An image taken at a distance. The affected area is the leg. Male contributor, age 30–39:
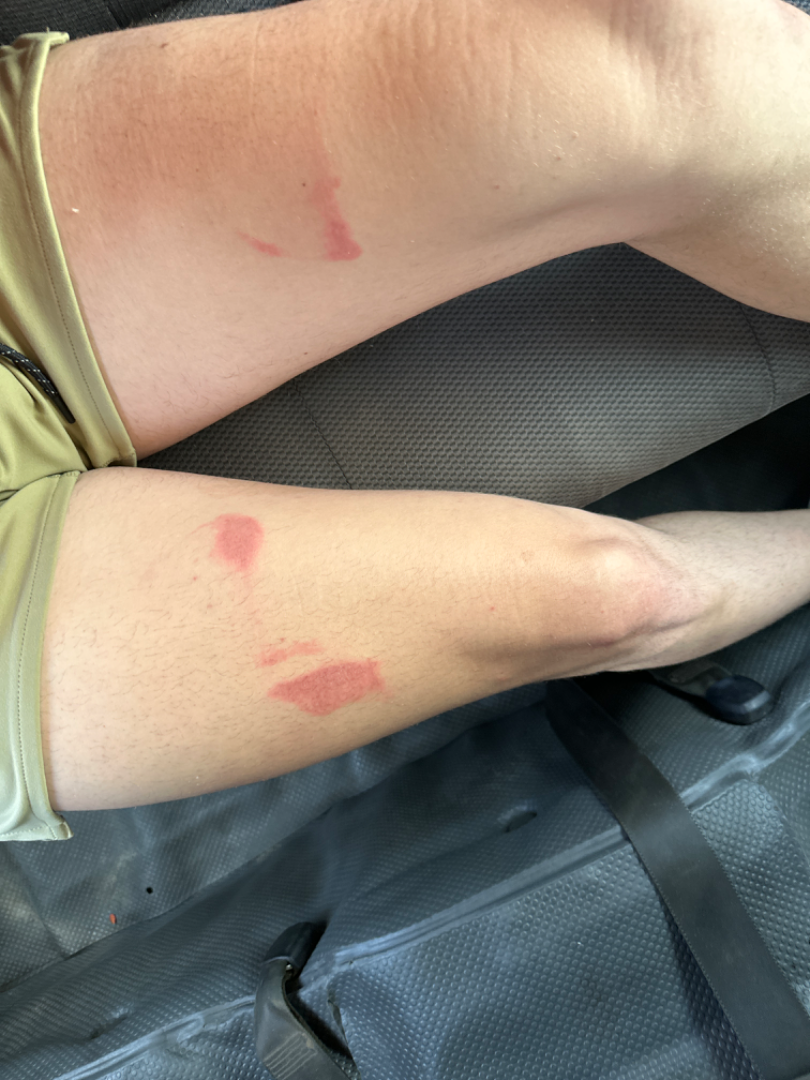- impression · the differential includes Abrasion and/or friction burn of thigh without infection and Irritant Contact Dermatitis, with no clear leading consideration; less likely is Burn of skin; less probable is ecchymoses; a more distant consideration is Allergic Contact Dermatitis